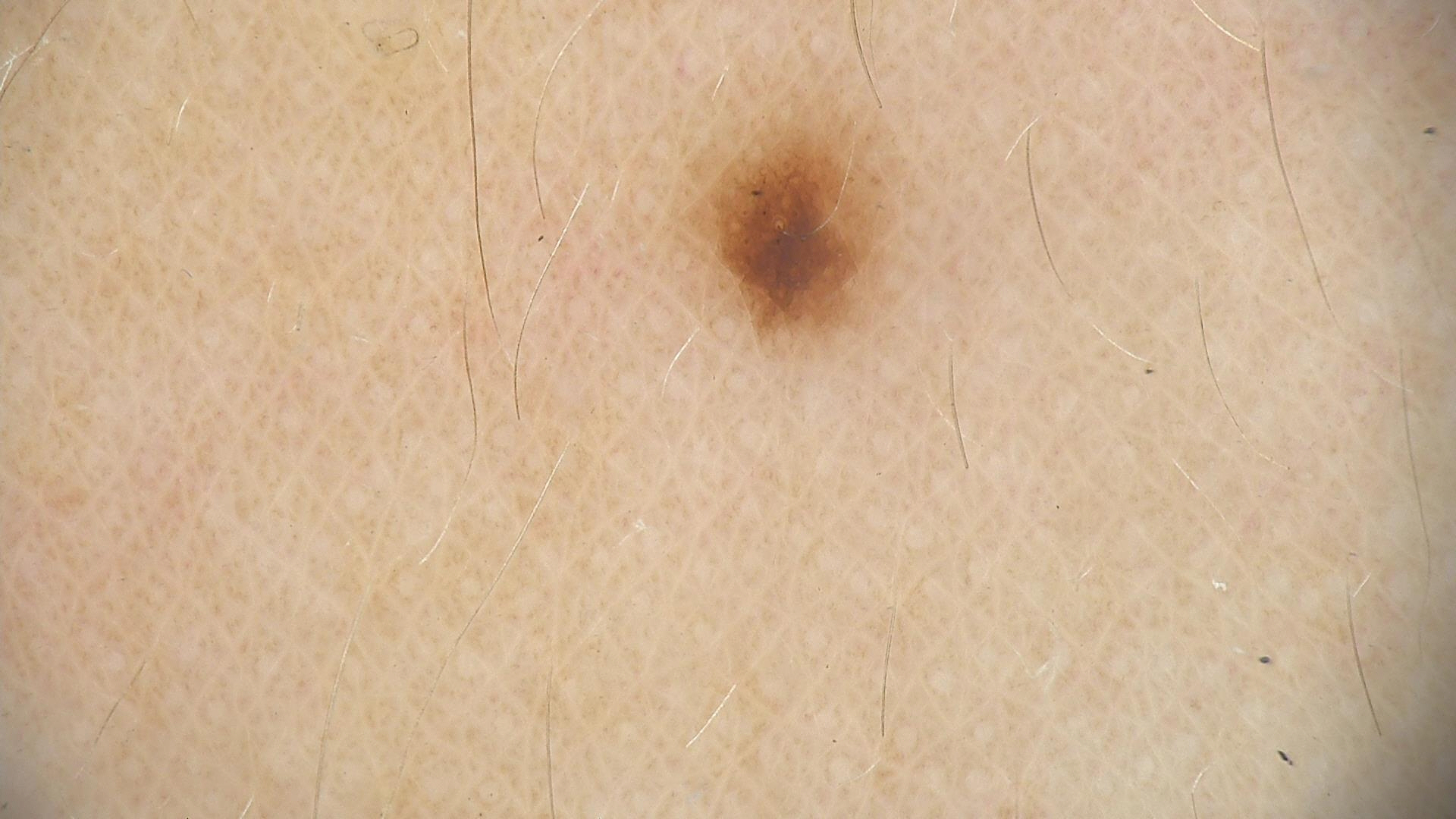image: dermatoscopy
diagnosis:
  name: dysplastic junctional nevus
  code: jd
  malignancy: benign
  super_class: melanocytic
  confirmation: expert consensus